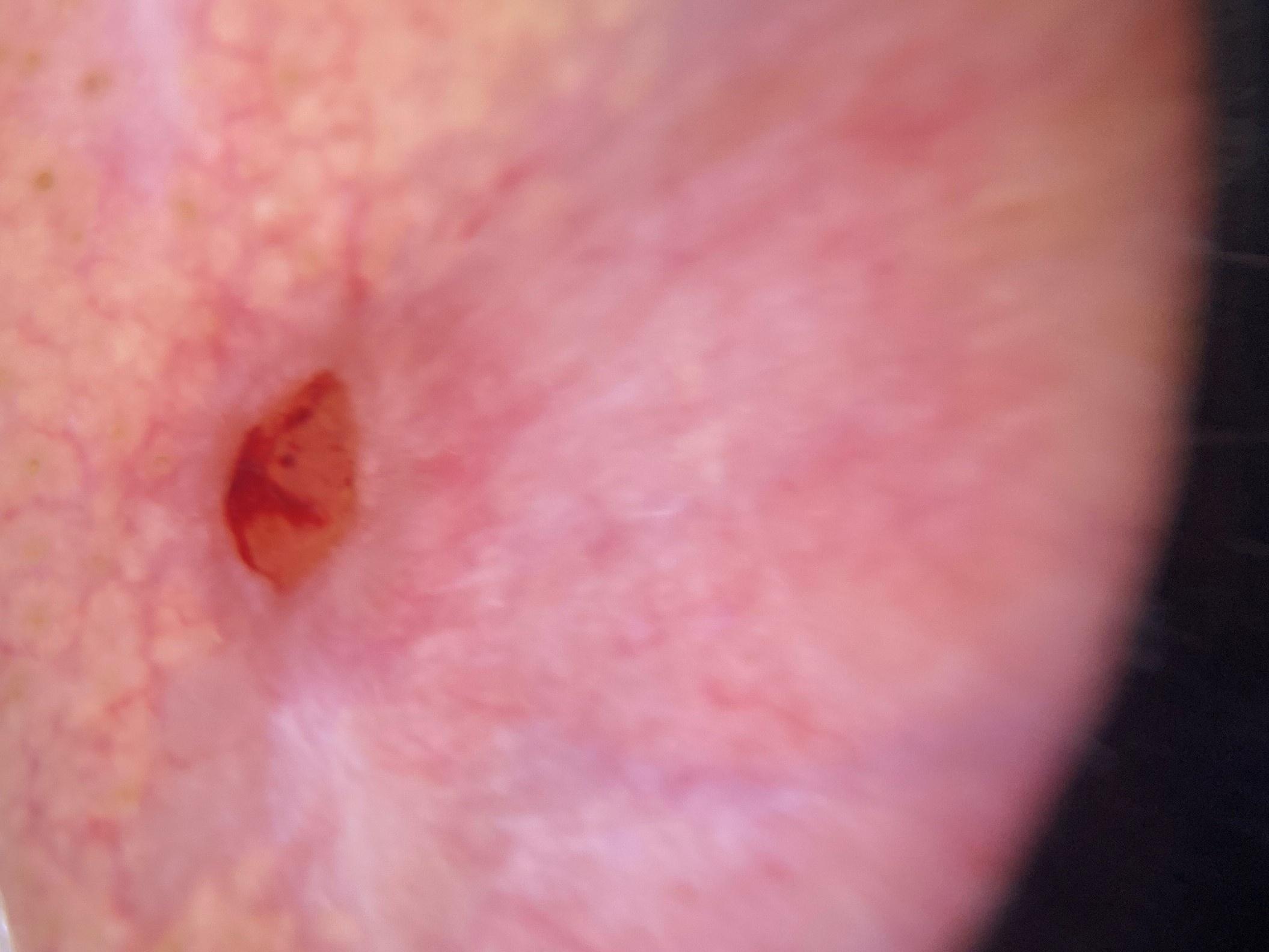A male subject aged around 80.
The chart documents a previous melanoma but no melanoma in first-degree relatives.
A dermoscopic close-up of a skin lesion.
The lesion was found on the head or neck.
Histopathologically confirmed as a malignant, adnexal lesion — a basal cell carcinoma.